Texture is reported as raised or bumpy; reported duration is one to four weeks; no associated lesion symptoms were reported; the photograph was taken at an angle; no associated systemic symptoms reported; male contributor, age 18–29; the lesion involves the leg, arm and head or neck; self-categorized by the patient as a rash — 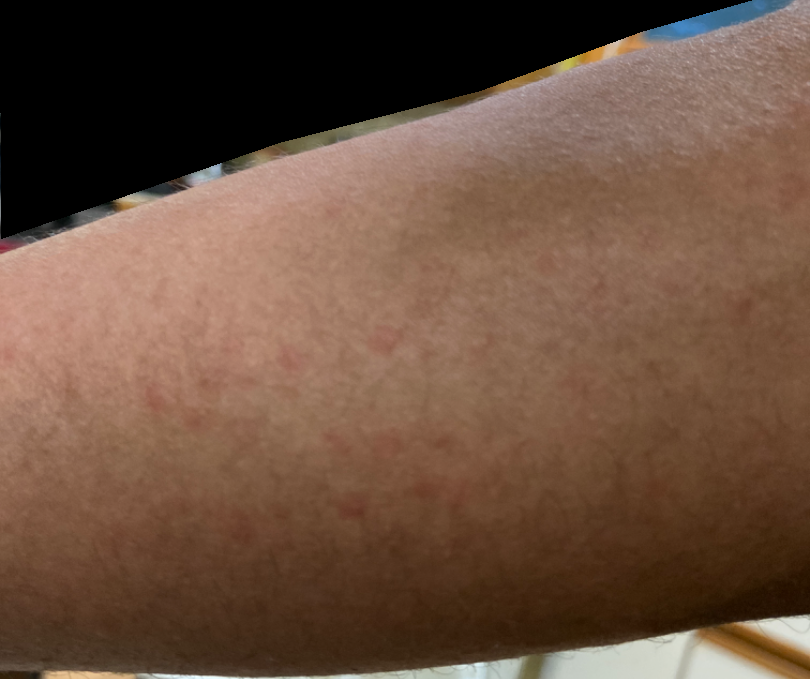The skin condition could not be confidently assessed from this image.